Reported duration is about one day; located on the leg; the patient described the issue as a rash; the lesion is described as flat; symptoms reported: itching; the photograph is a close-up of the affected area.
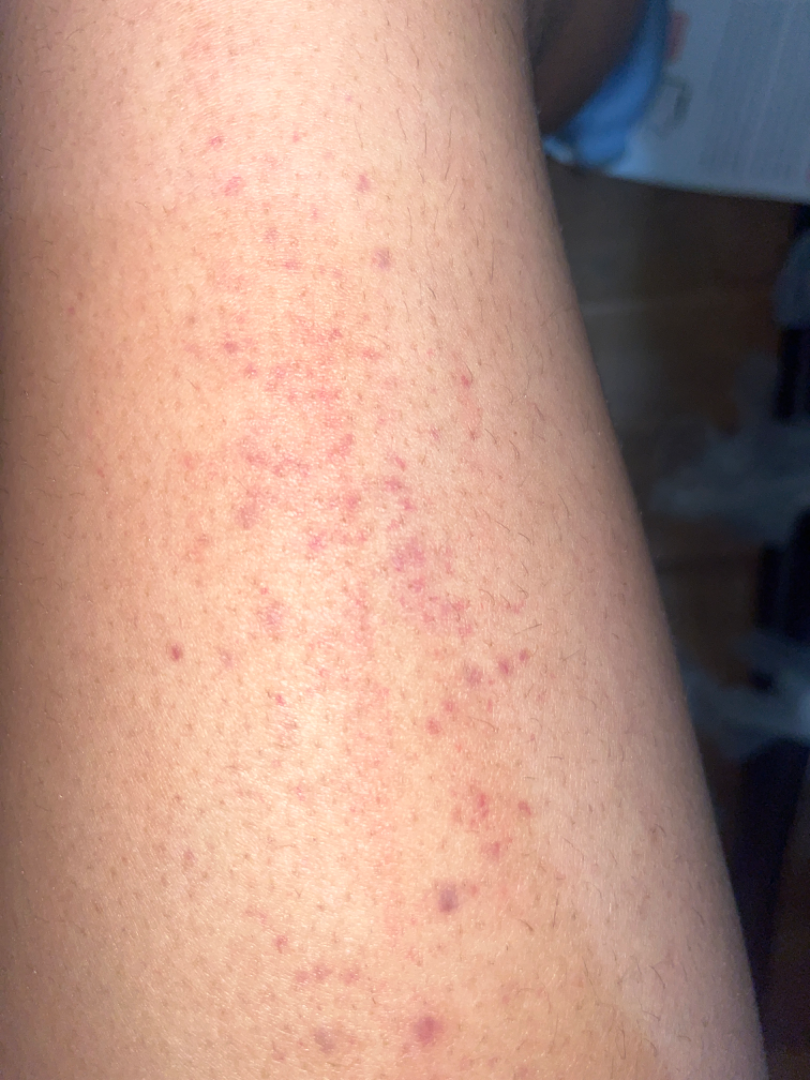The dermatologist could not determine a likely condition from the photograph alone.